Dermoscopy of a skin lesion; the patient says their skin tans without first burning; a moderate number of moles by the patient's own estimate; a male patient 72 years old; collected as part of a research study, without a referral diagnosis — 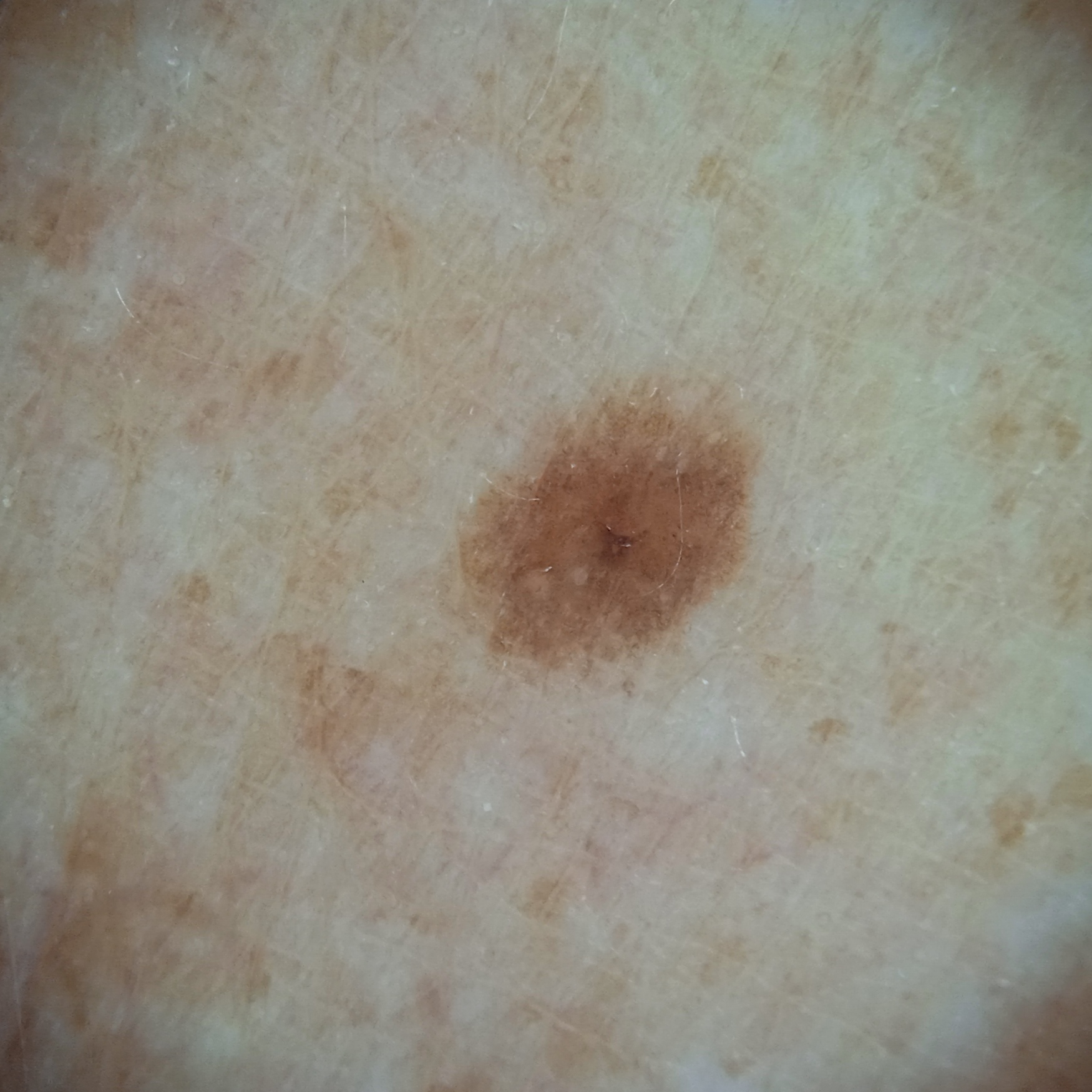- body site — the back
- diameter — 3.7 mm
- diagnosis — melanocytic nevus (dermatologist consensus)